A dermoscopy image of a single skin lesion.
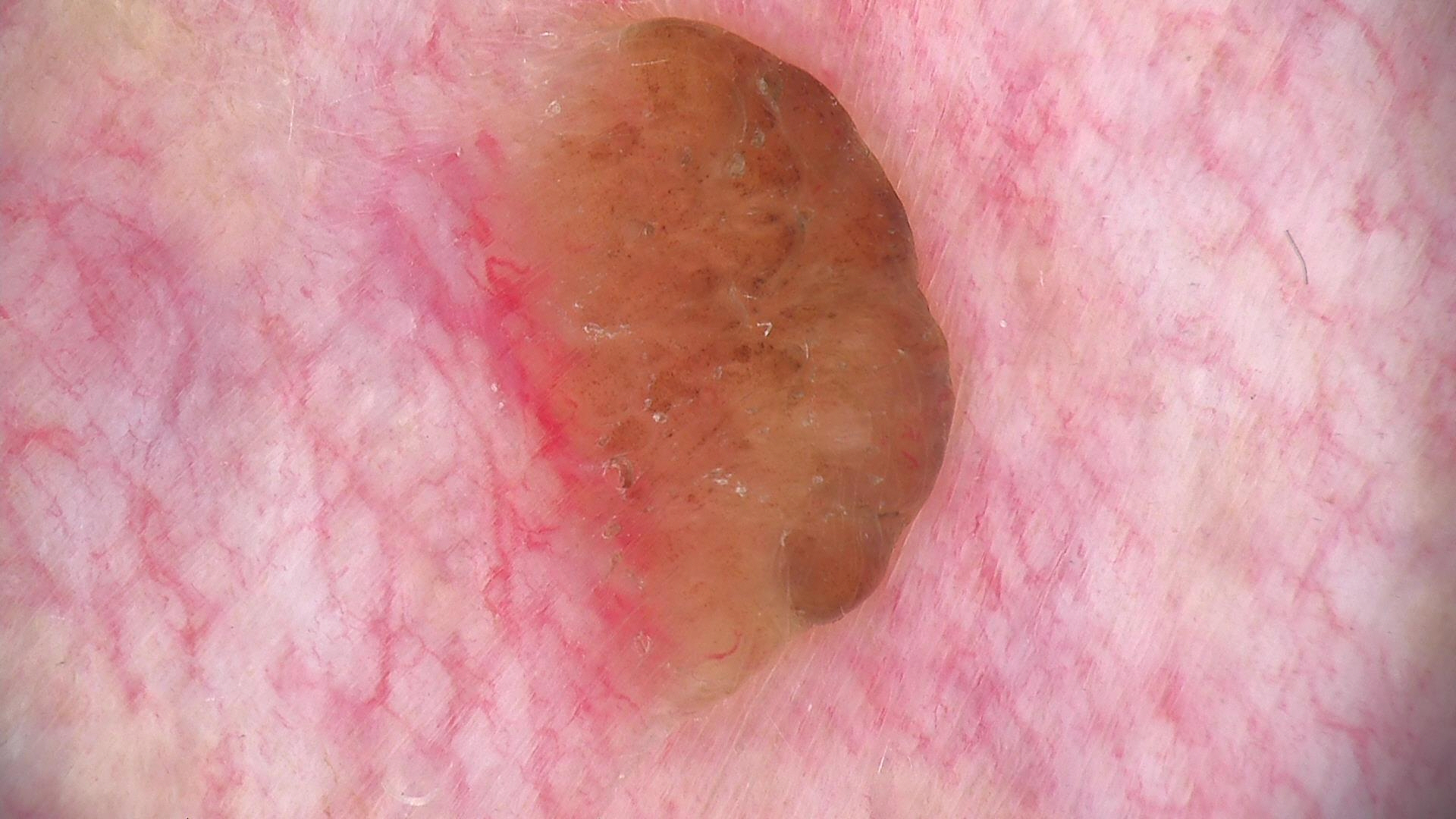diagnostic label: dermal nevus (expert consensus).